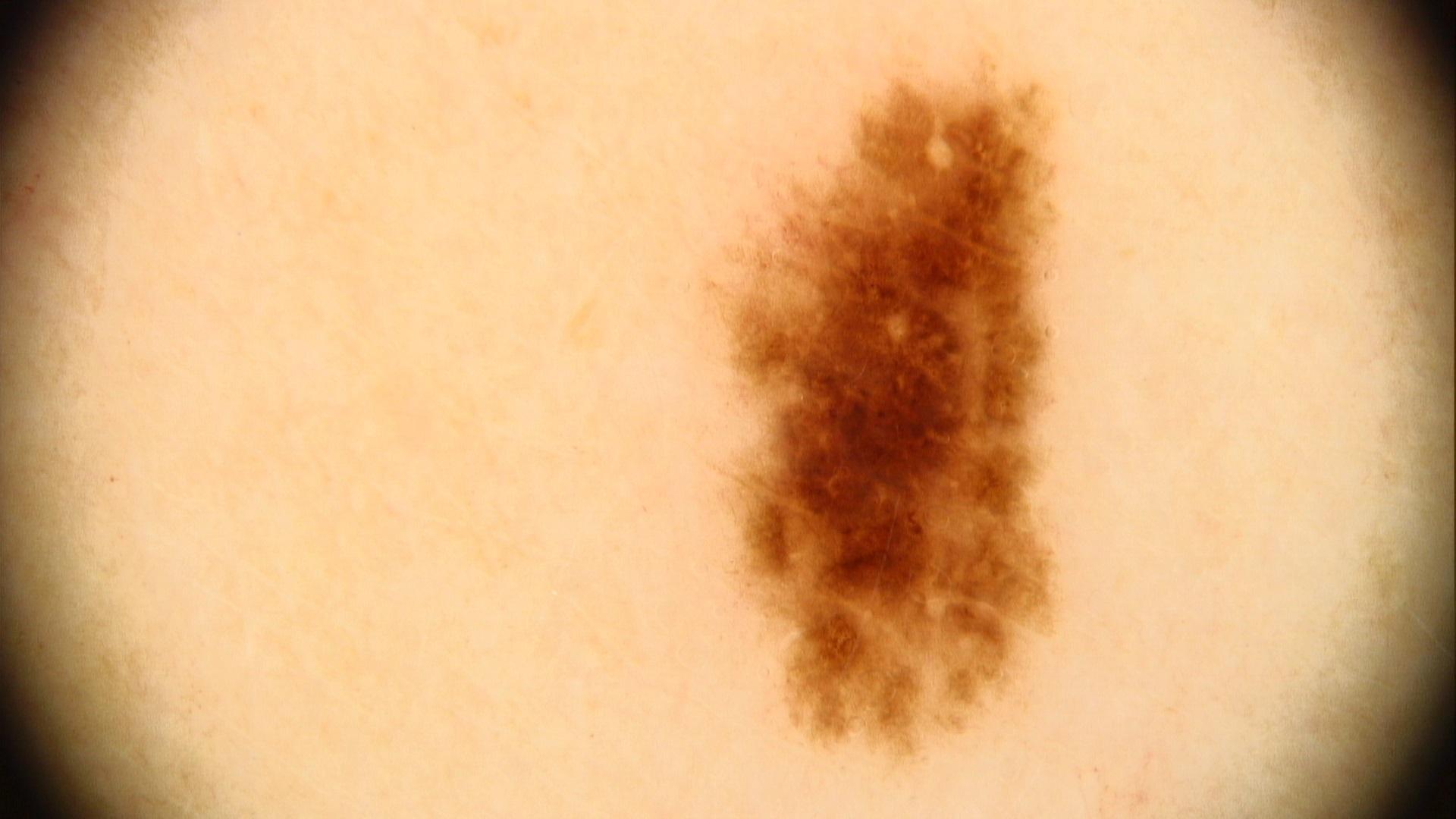The chart records a first-degree relative with melanoma but no prior melanoma.
The patient is Fitzpatrick skin type III.
A dermoscopic image of a skin lesion.
A male patient approximately 40 years of age.
The lesion involves the trunk.
The diagnostic impression was a benign lesion — a nevus.